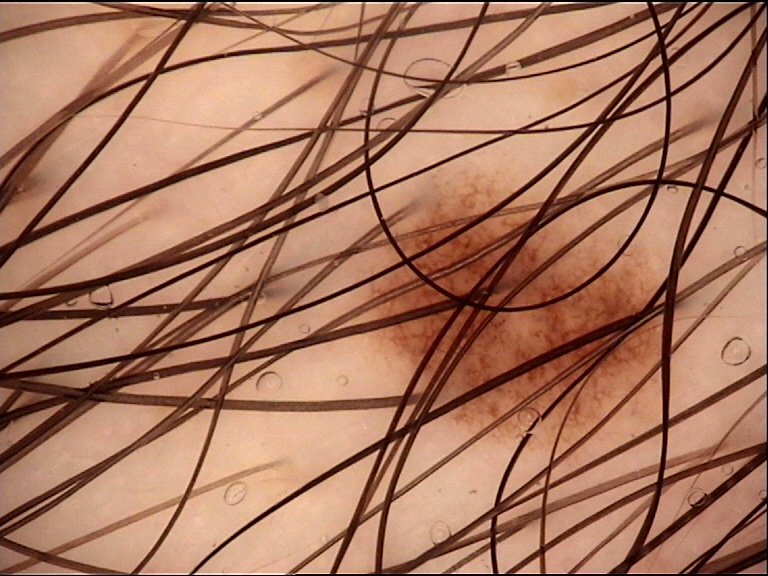A dermatoscopic image of a skin lesion.
Diagnosed as a dysplastic junctional nevus.